A skin lesion imaged with a dermatoscope — 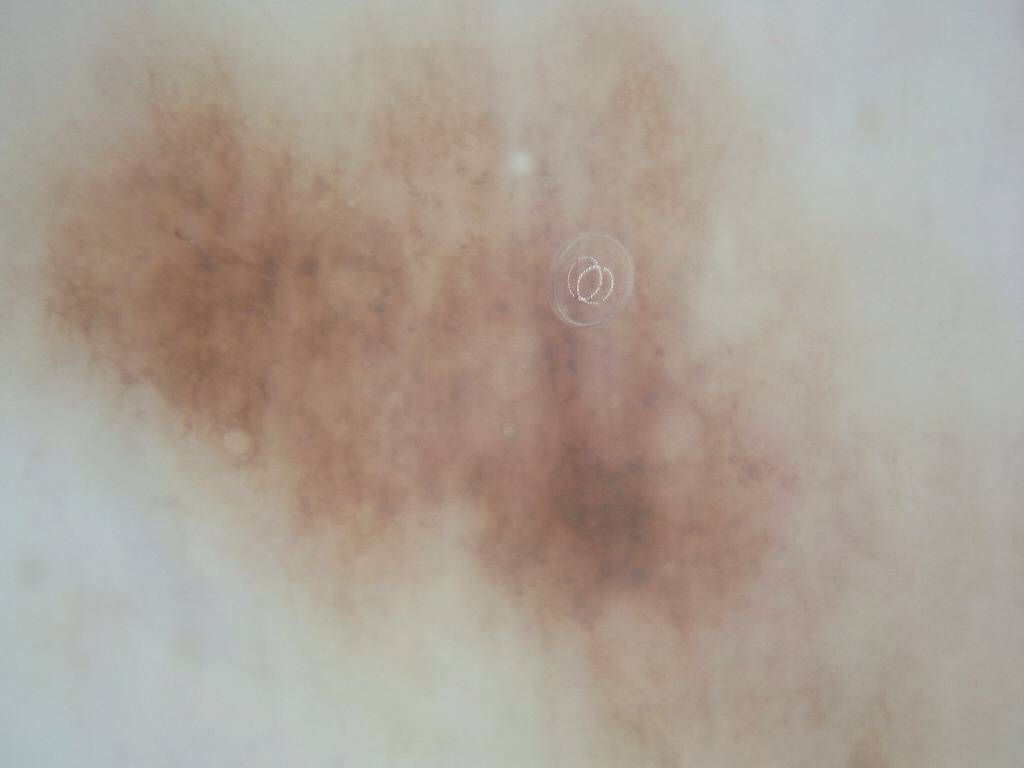Image and clinical context: The lesion spans essentially the entire dermoscopic field. Conclusion: Histopathology confirmed a skin cancer.